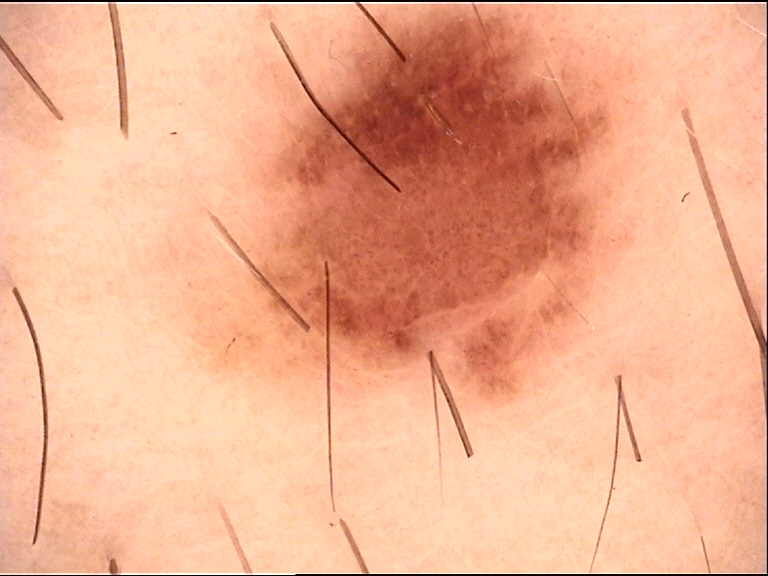Case:
* modality: dermatoscopy
* diagnostic label: dysplastic junctional nevus (expert consensus)